Self-categorized by the patient as a rash · symptoms reported: itching and enlargement · the contributor notes the lesion is flat · a close-up photograph · reported duration is one to four weeks · the subject is a female aged 50–59 · no relevant systemic symptoms — 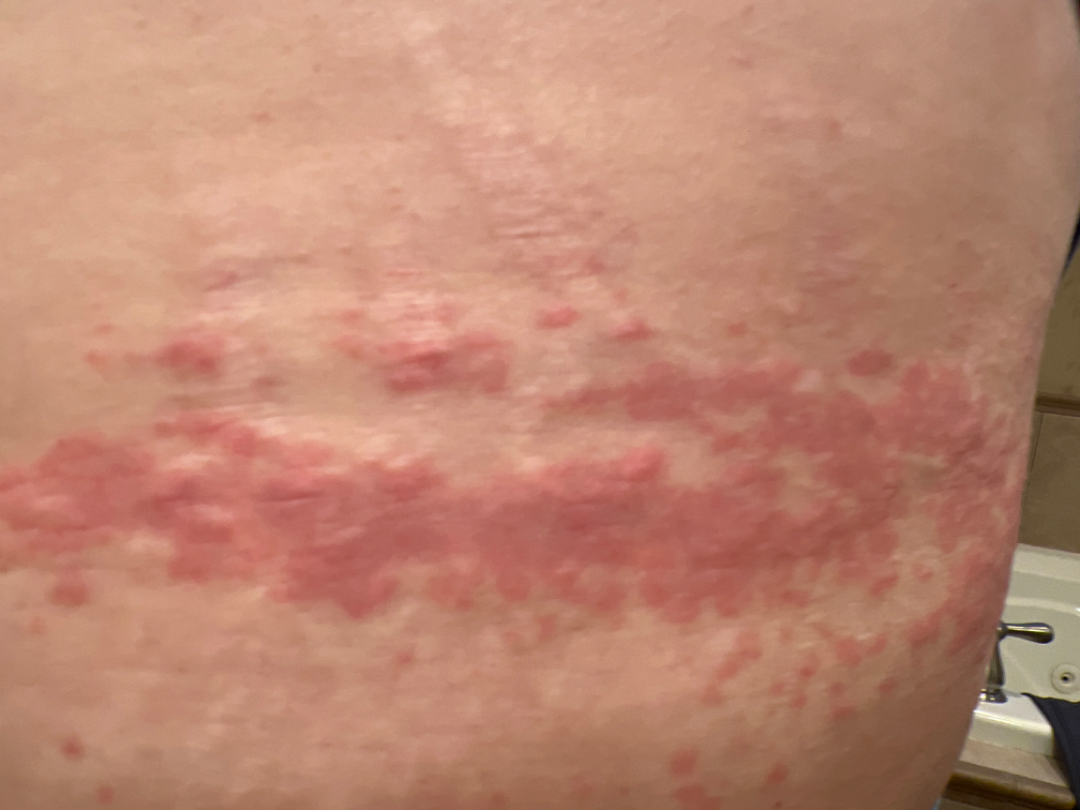Impression: The reviewing dermatologist's impression was: most consistent with Allergic Contact Dermatitis.